The contributor is 40–49, female · located on the arm · close-up view: 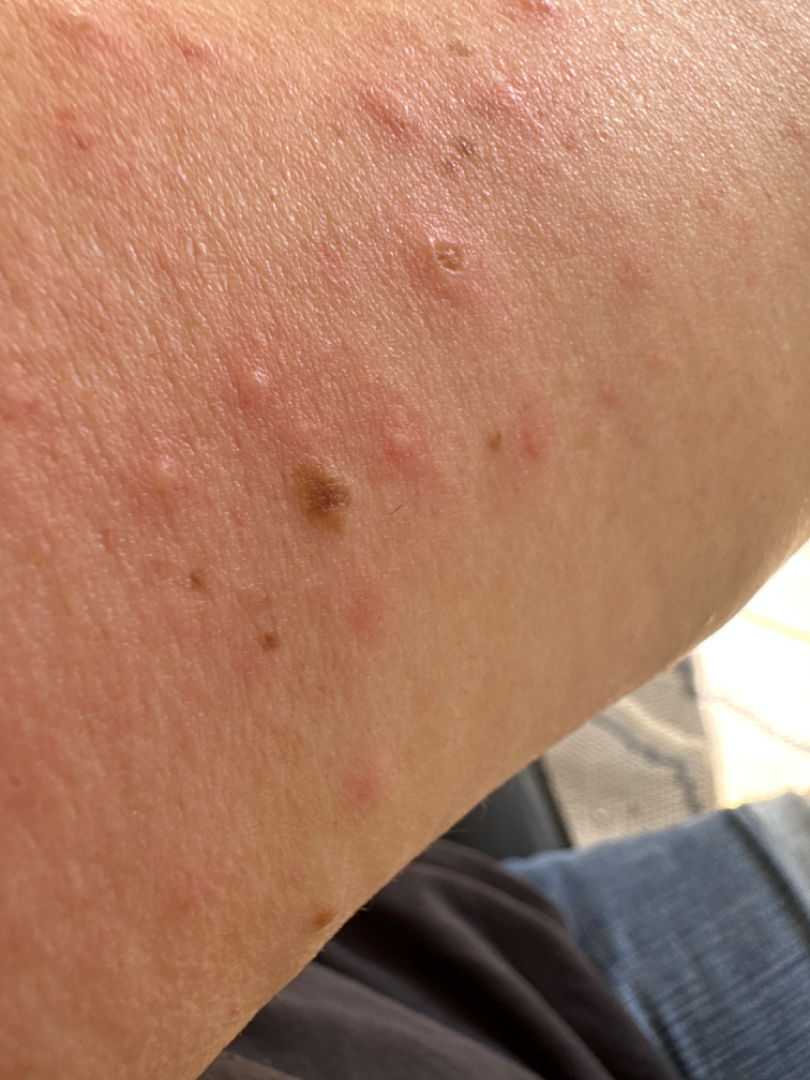diagnostic considerations=favoring Acute dermatitis, NOS; less likely is Scabies; less probable is Folliculitis; lower on the differential is Herpes Zoster; a more distant consideration is Drug Rash; a remote consideration is Eczema; less likely is Allergic Contact Dermatitis.